A skin lesion imaged with a dermatoscope: 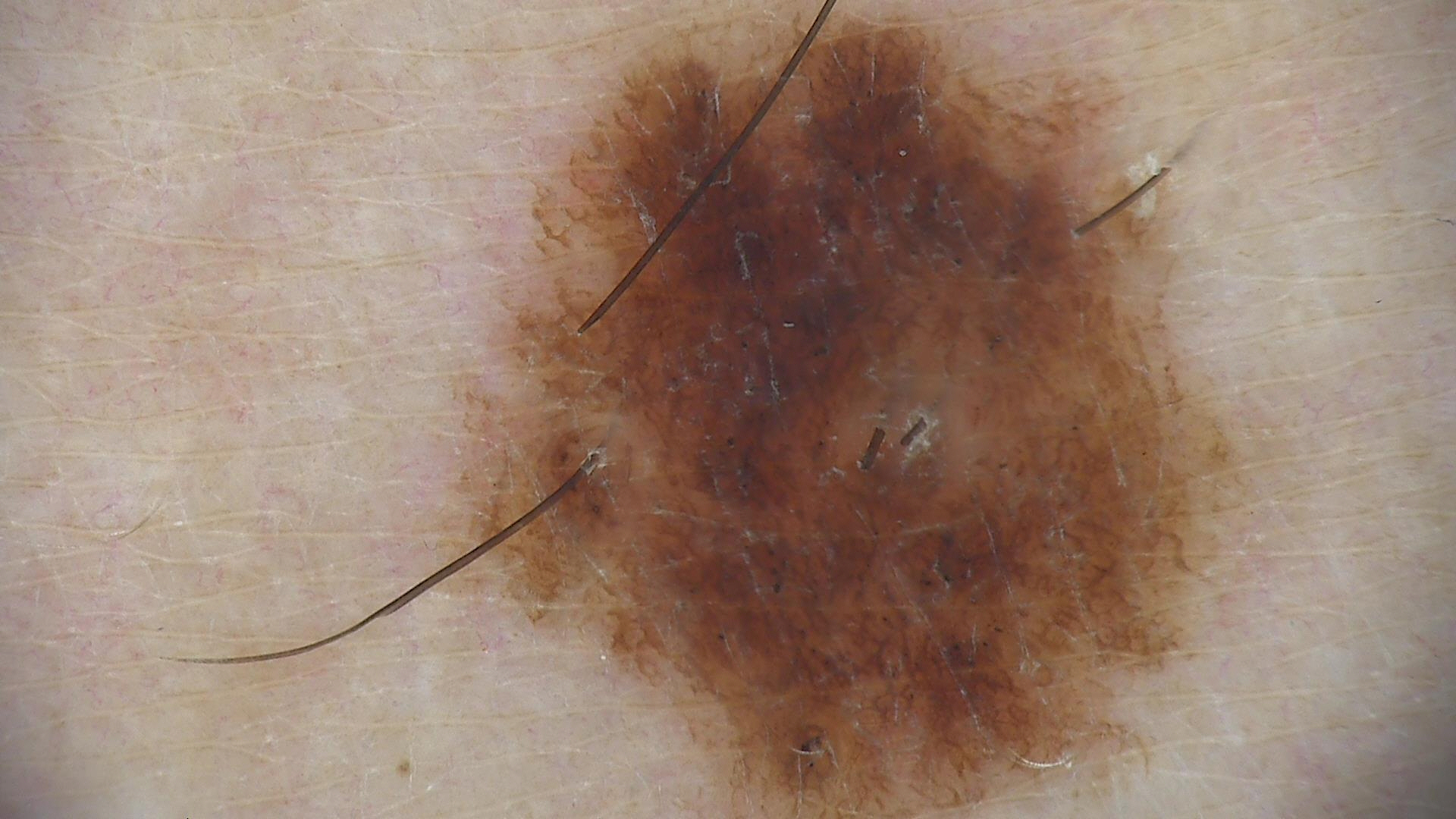The diagnosis was a benign lesion — a dysplastic junctional nevus.